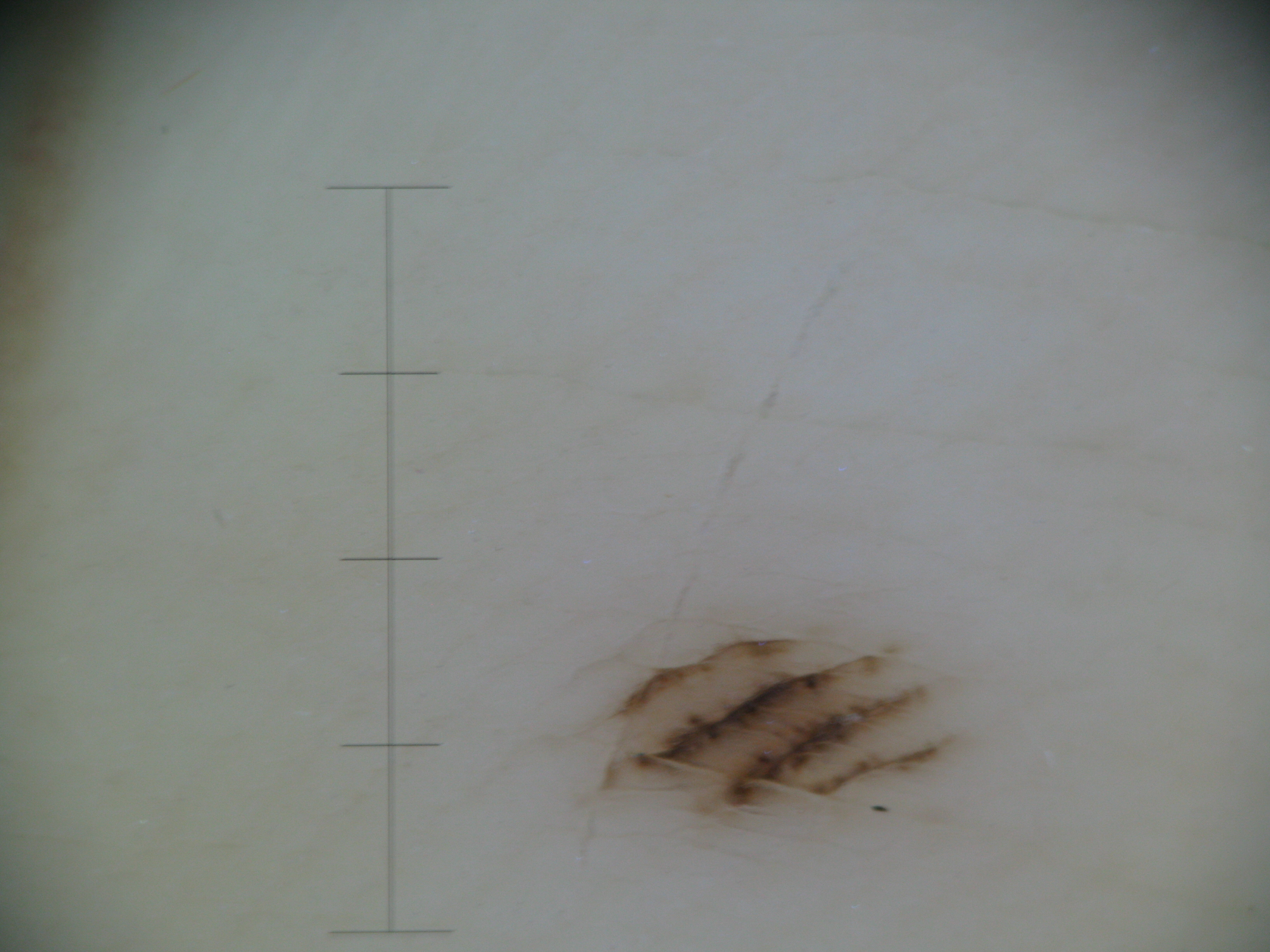Dermoscopy of a skin lesion. The morphology is that of a banal lesion. The diagnosis was an acral junctional nevus.